By history, alcohol use, prior malignancy (patient or family), and prior skin cancer (patient or family) · the patient was assessed as FST III · a clinical close-up photograph of a skin lesion · a female patient 56 years old:
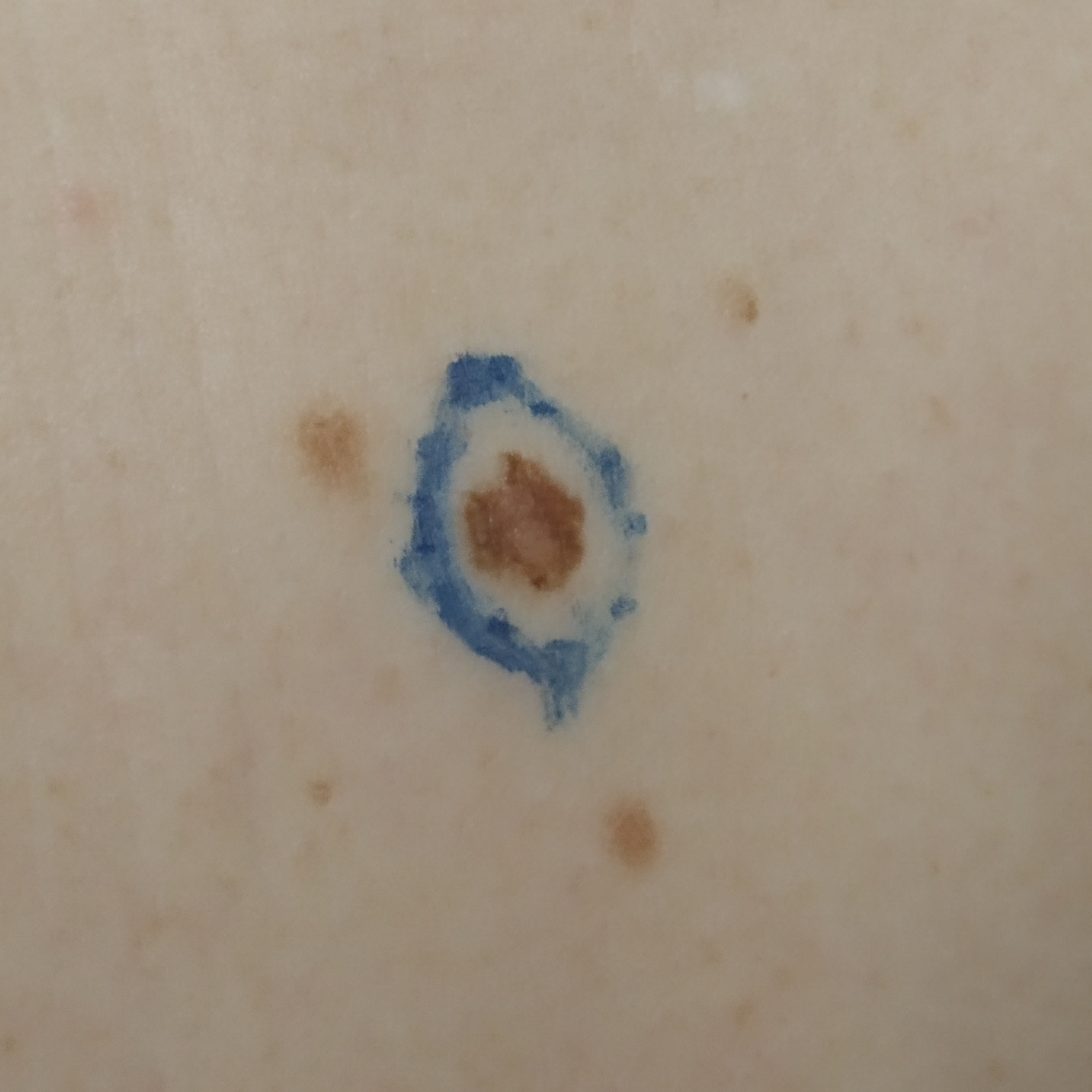Case summary:
The lesion involves the abdomen. The lesion measures approximately 5 × 4 mm. Per patient report, the lesion does not hurt.
Conclusion:
Histopathological examination showed a benign lesion — a nevus.